The photo was captured at an angle · the lesion involves the palm — 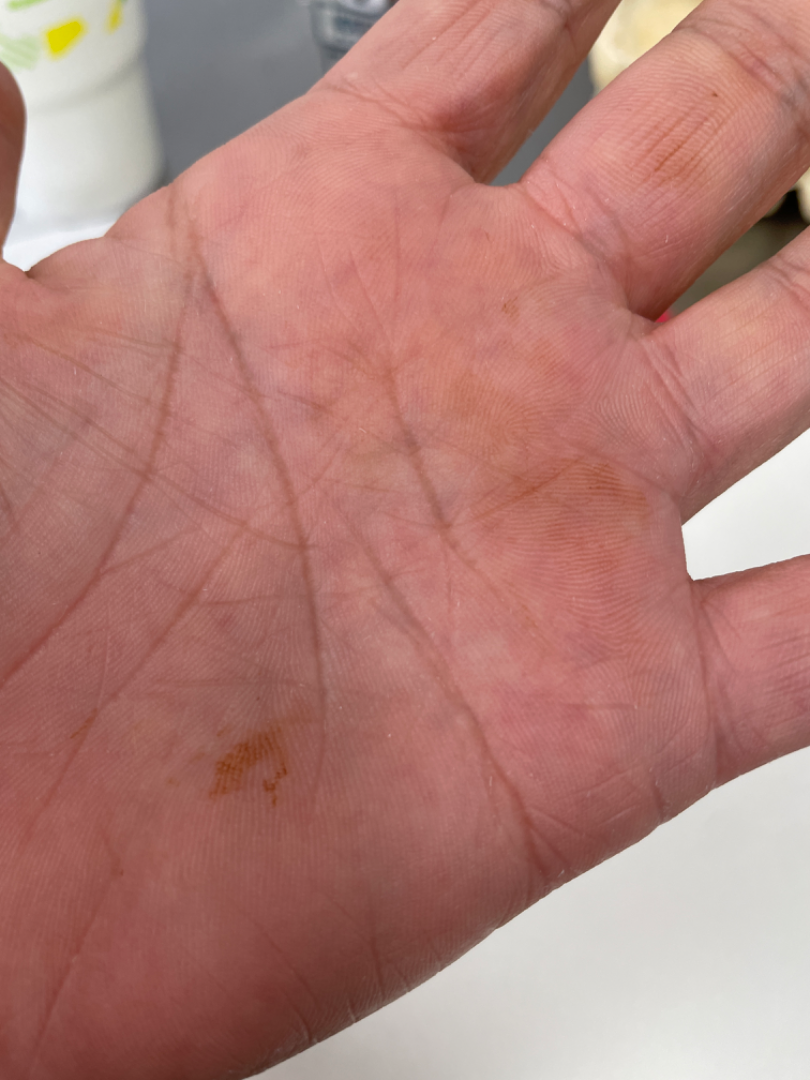Diagnostic features were not clearly distinguishable in this photograph.